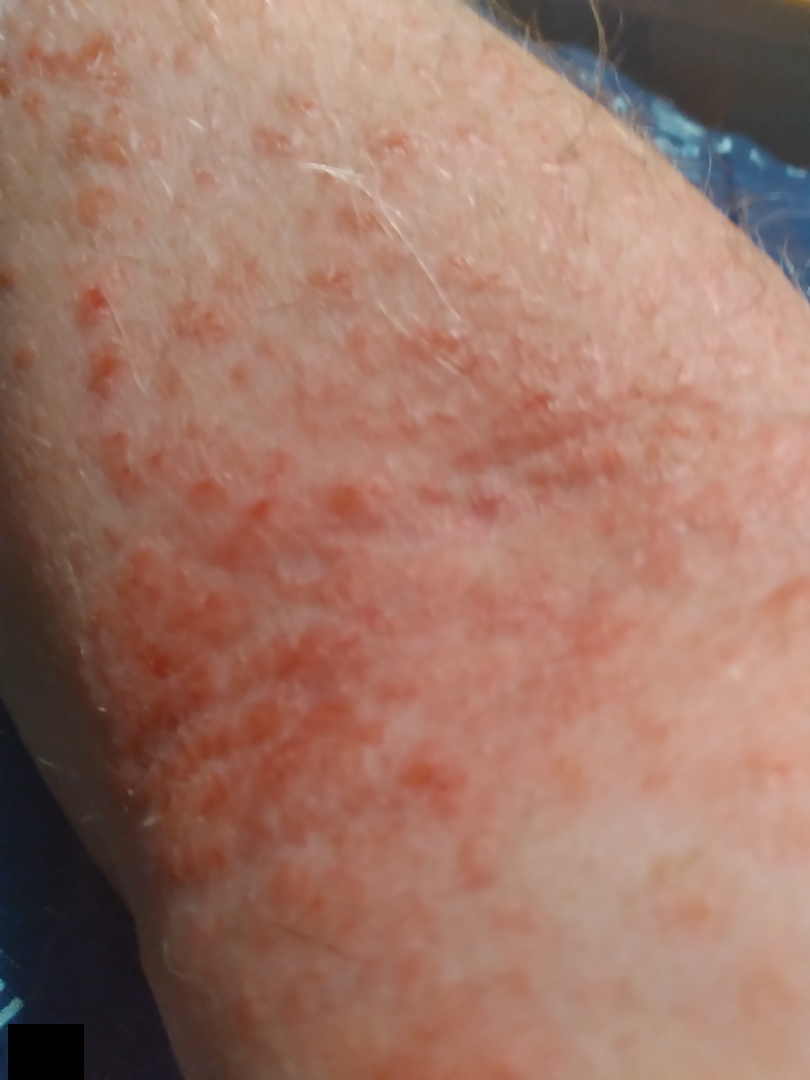{
  "differential": {
    "tied_lead": [
      "Tinea",
      "Eczema",
      "Allergic Contact Dermatitis"
    ]
  }
}